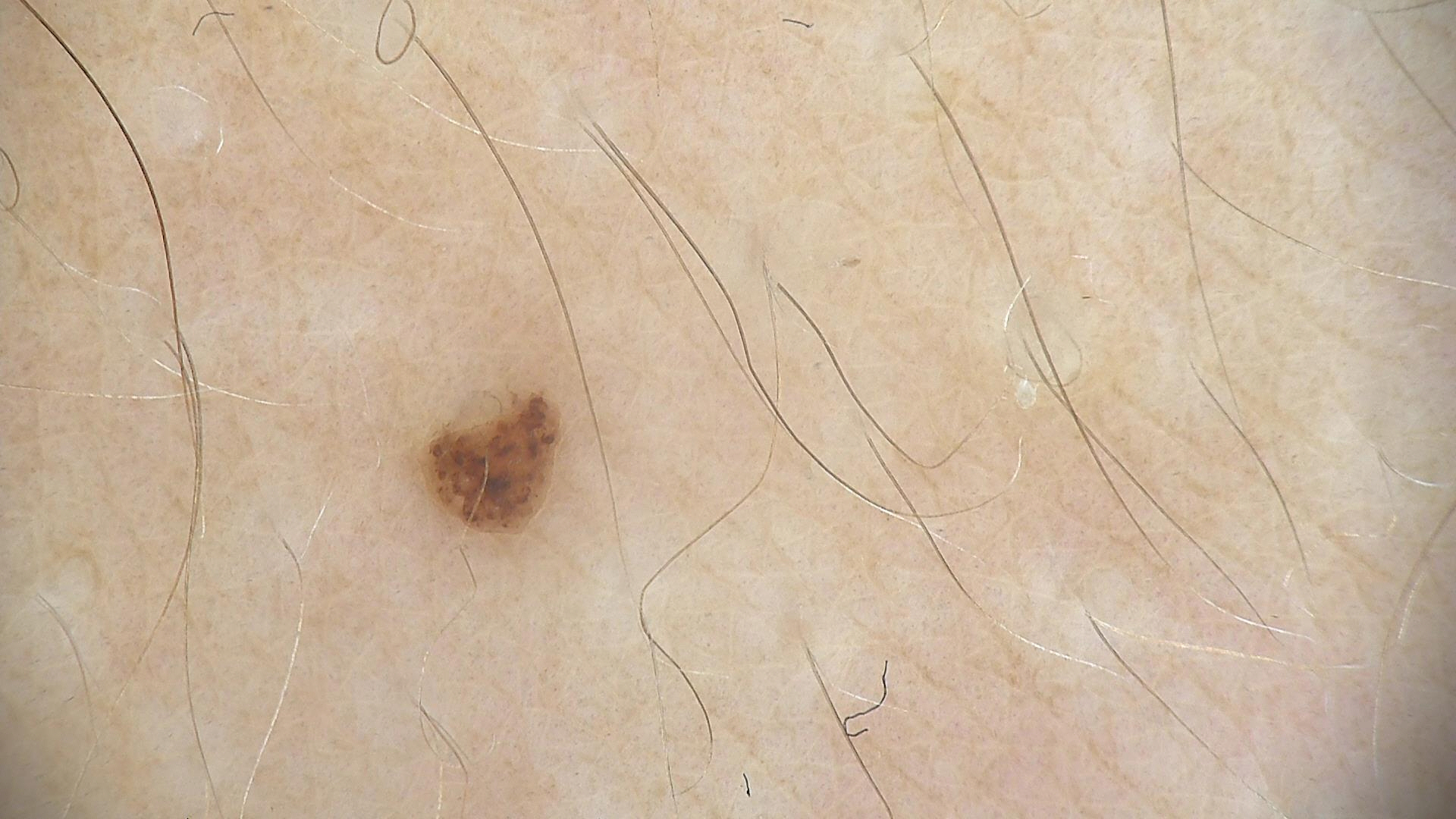imaging: dermatoscopy; diagnosis: dysplastic junctional nevus (expert consensus).